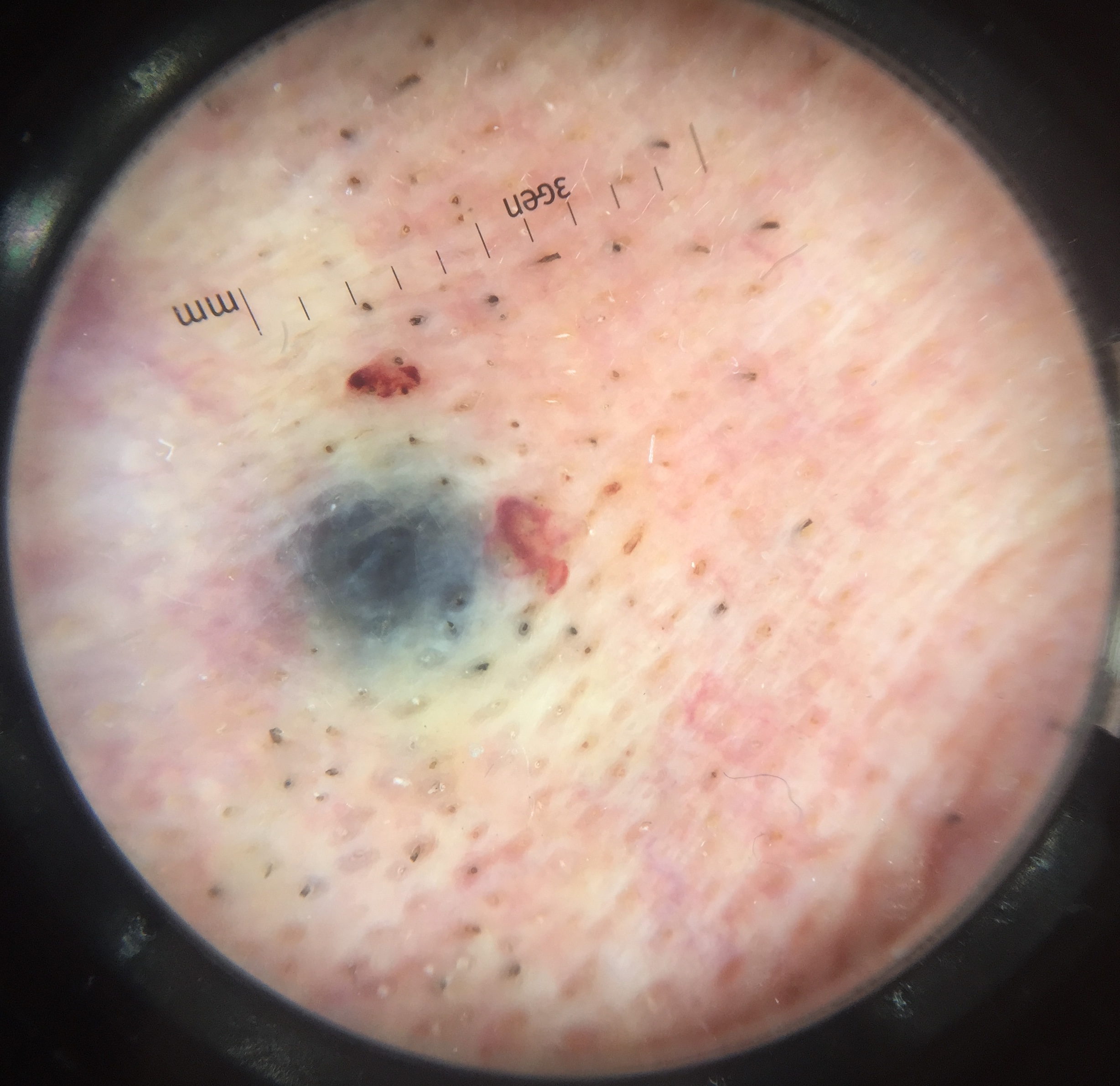class = blue nevus (expert consensus).